A patient 52 years old: 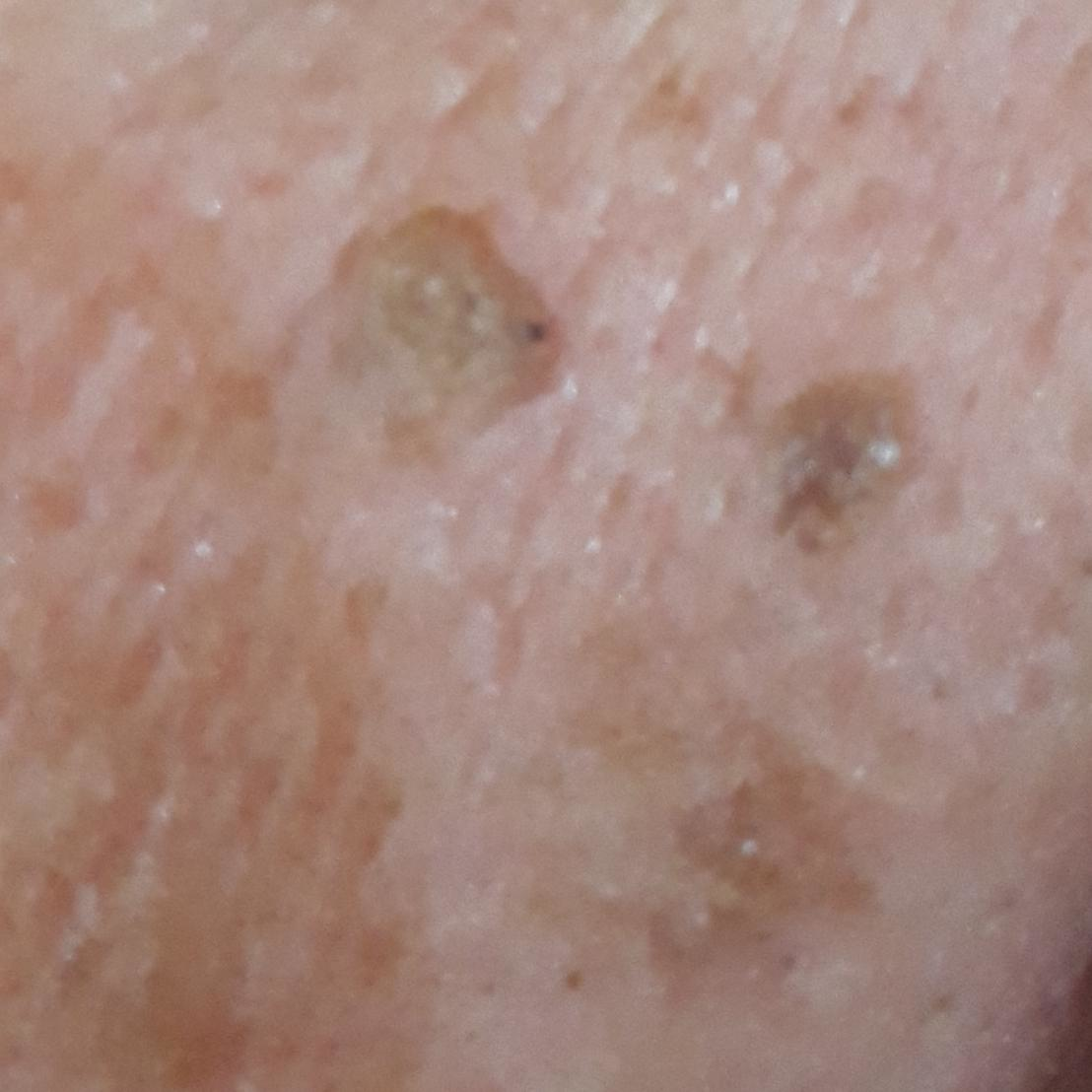The patient describes that the lesion has grown and is elevated. The consensus clinical diagnosis was a benign lesion — a seborrheic keratosis.